The affected area is the back of the hand and arm, the patient is a male aged 30–39, a close-up photograph: 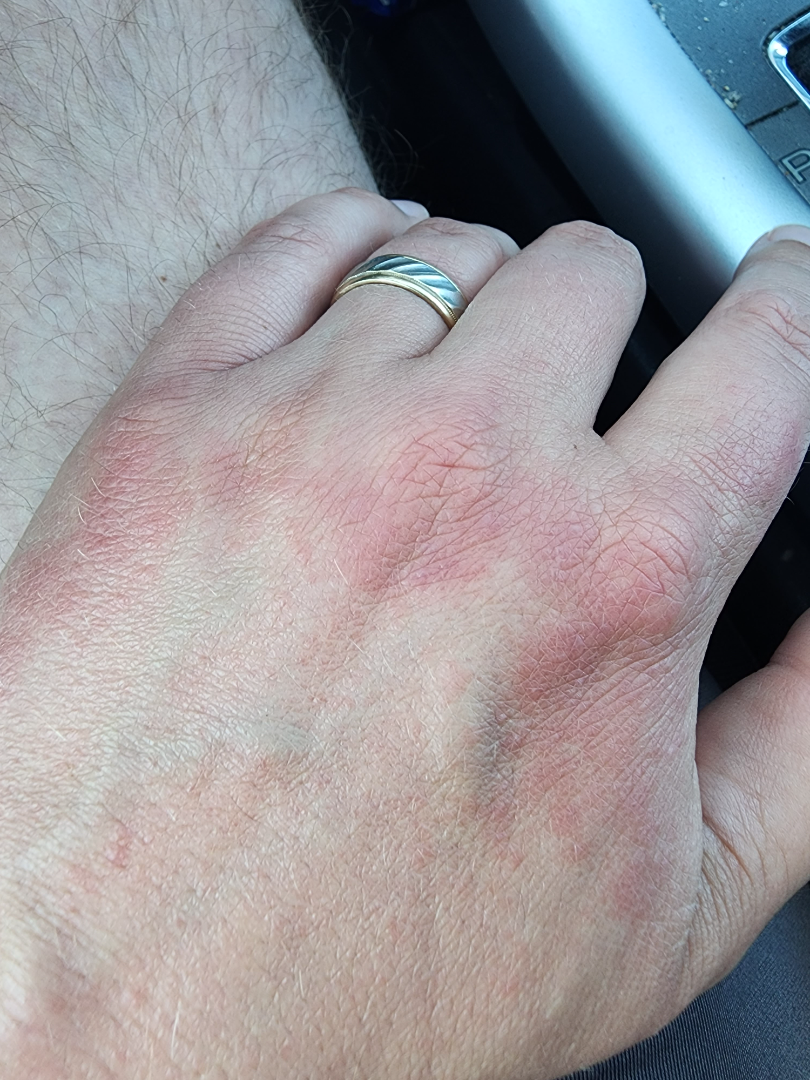{
  "duration": "one to four weeks",
  "patient_category": "a rash",
  "differential": {
    "leading": [
      "Irritant Contact Dermatitis"
    ]
  }
}